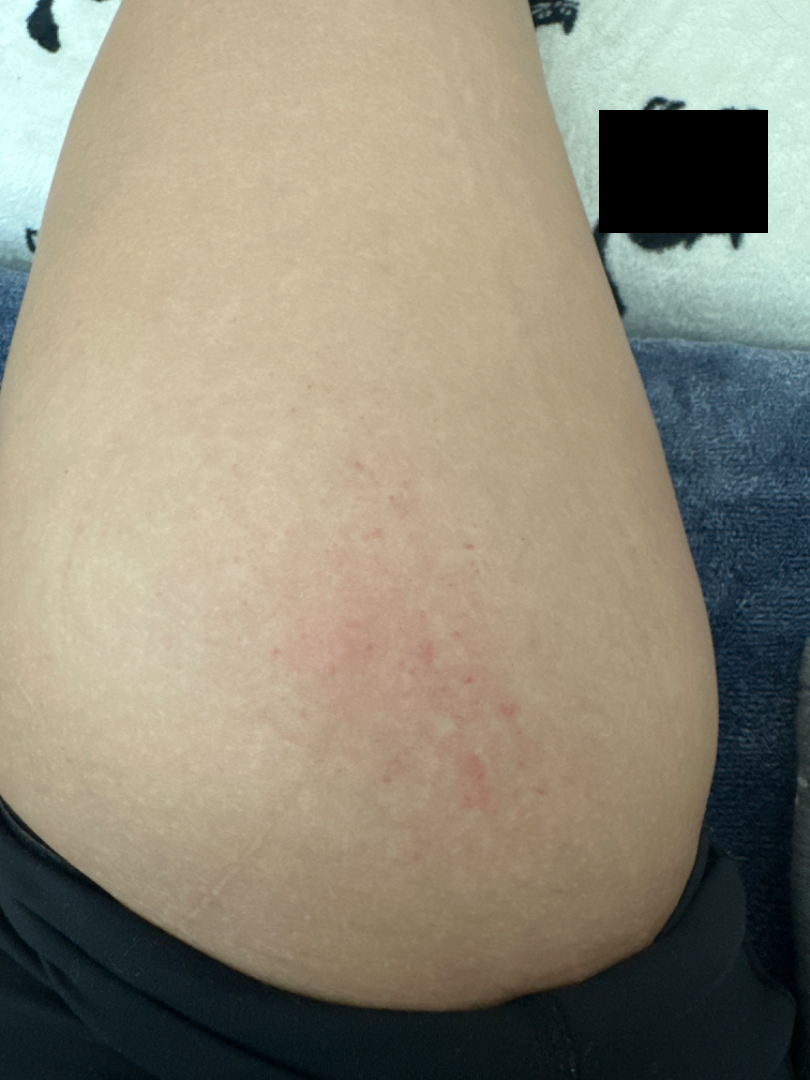| key | value |
|---|---|
| assessment | could not be assessed |